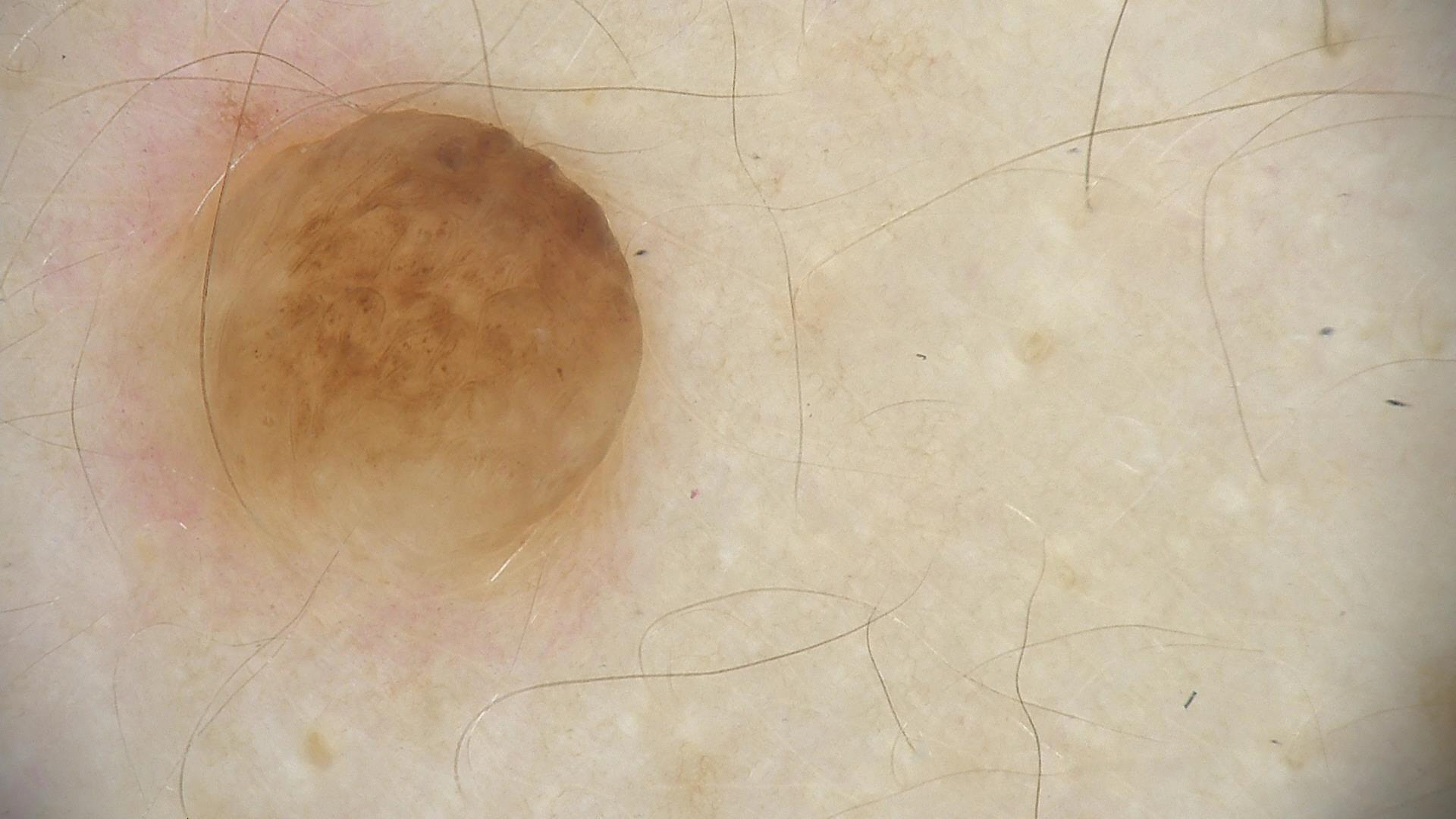* modality · dermatoscopy
* classification · banal
* class · dermal nevus (expert consensus)